The photograph was taken at a distance. The leg and arm are involved. The patient indicates the condition has been present for less than one week. The patient indicates pain, itching and burning. The patient indicates the lesion is raised or bumpy:
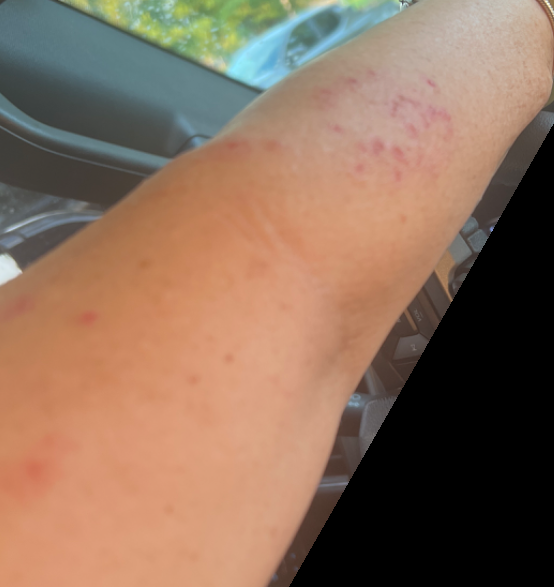• clinical impression: Tinea (33%); Insect Bite (33%); Allergic Contact Dermatitis (33%)